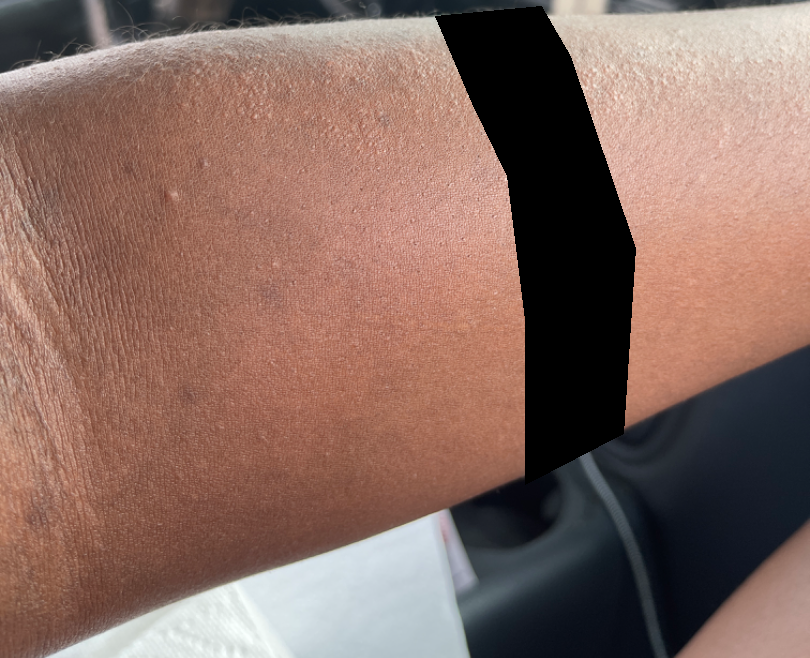The subject is a female aged 30–39.
The photograph was taken at an angle.
Present for one to four weeks.
No relevant systemic symptoms.
Texture is reported as raised or bumpy and rough or flaky.
Reported lesion symptoms include bothersome appearance and itching.
The arm is involved.
The differential includes Eczema and Allergic Contact Dermatitis, with no clear leading consideration.